A dermoscopic photograph of a skin lesion.
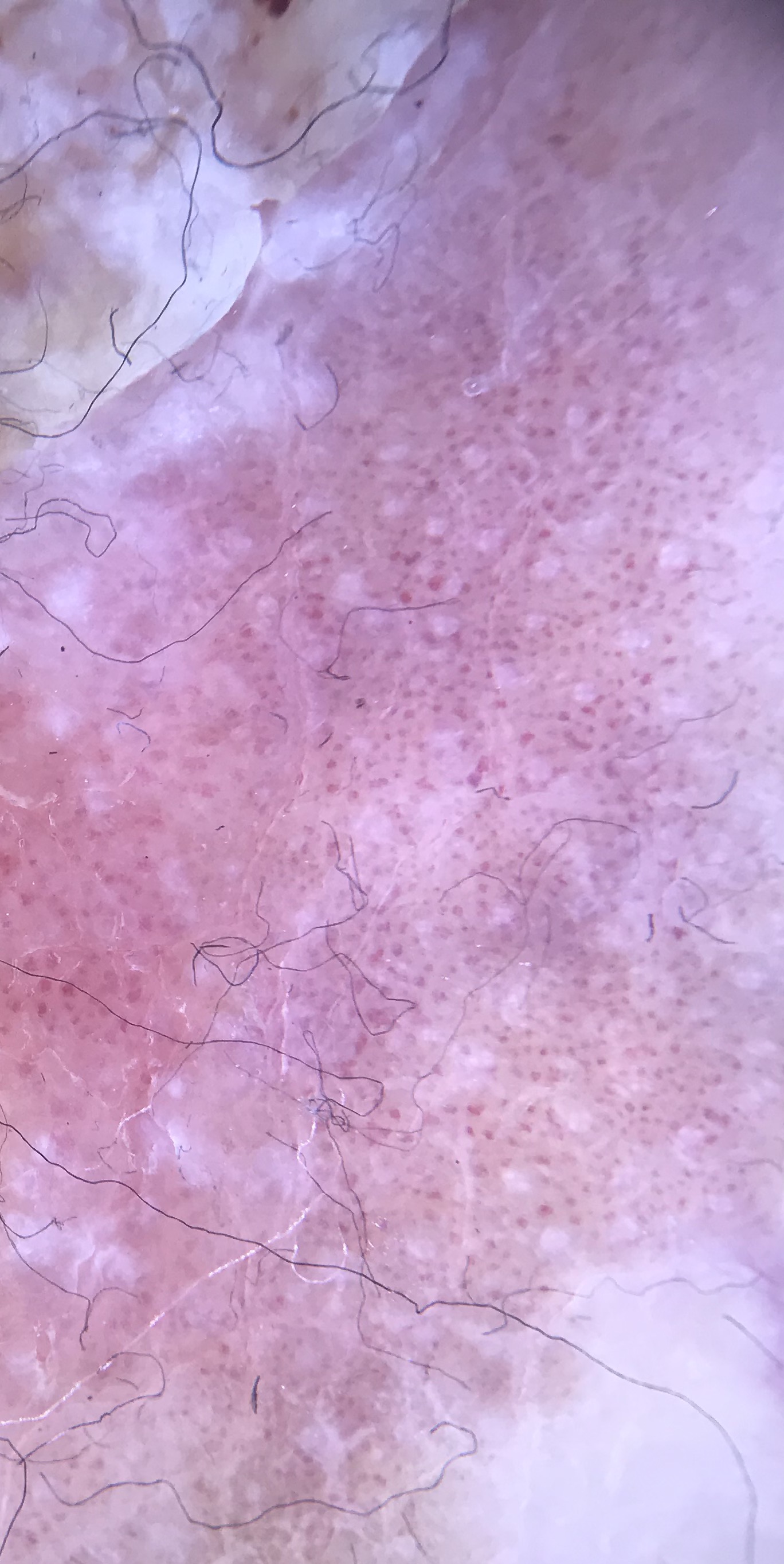Confirmed on histopathology as a keratinocytic, malignant lesion — Bowen's disease.